This image was taken at a distance. Female contributor, age 18–29: 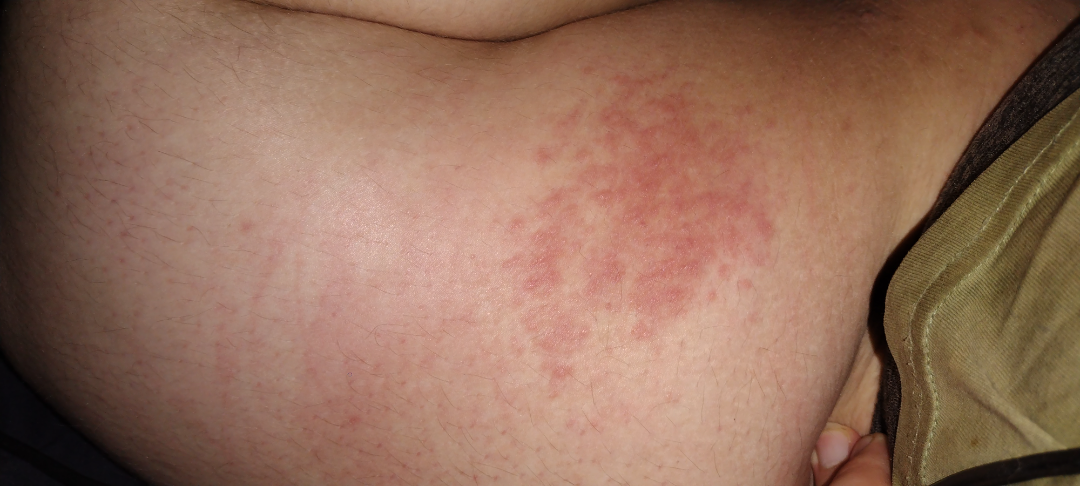Clinical context: Skin tone: Fitzpatrick phototype III; lay reviewers estimated Monk Skin Tone 2 or 3. The patient reports the condition has been present for more than one year. The lesion is associated with enlargement and itching. Texture is reported as raised or bumpy. The patient considered this a rash. Assessment: Eczema (possible); Allergic Contact Dermatitis (possible); Irritant Contact Dermatitis (possible).